A male patient age 15 · collected as part of a research study, without a referral diagnosis · few moles overall by the patient's own estimate · dermoscopy of a skin lesion:
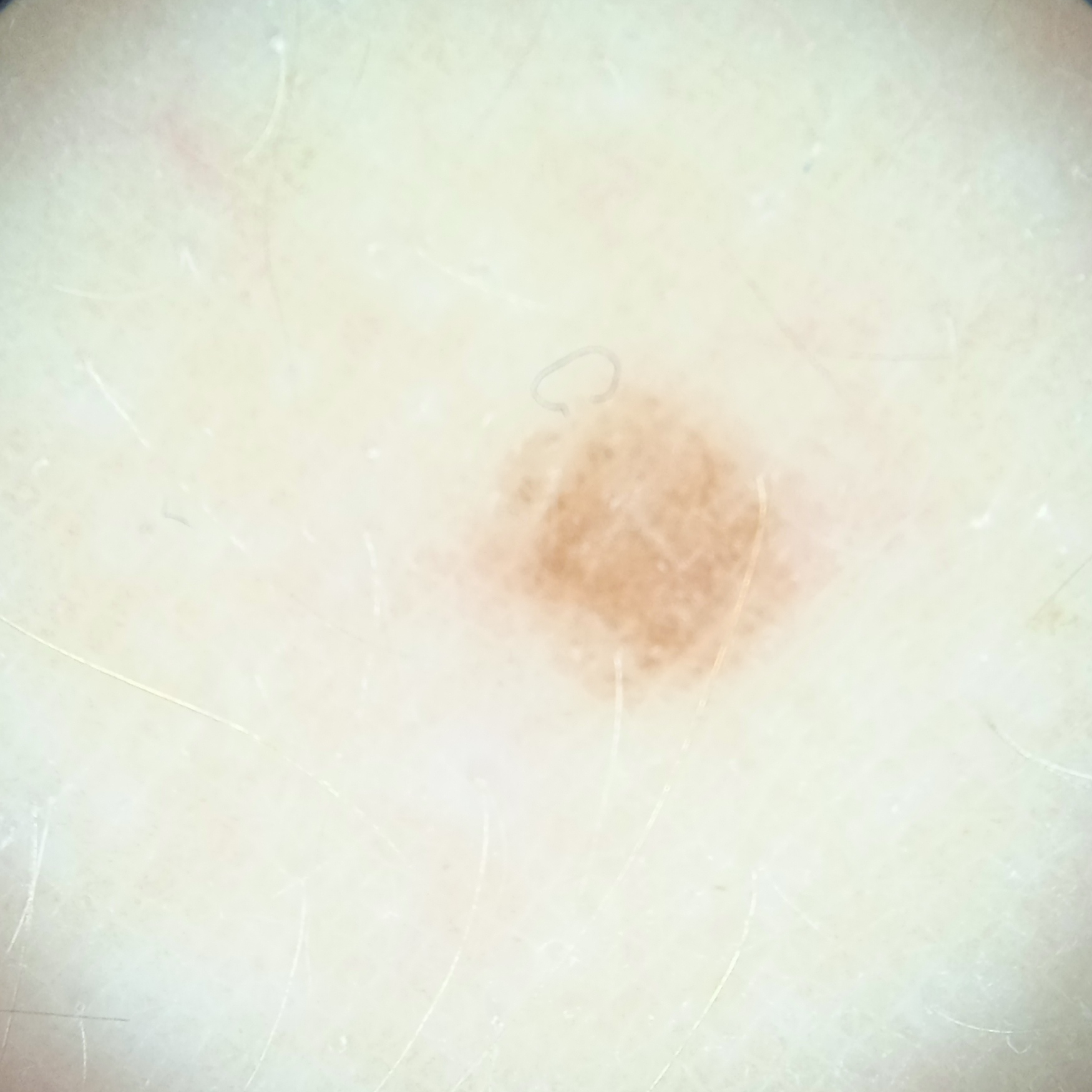Summary: Located on an arm. Measuring roughly 3.5 mm. Conclusion: The lesion was assessed as a melanocytic nevus.